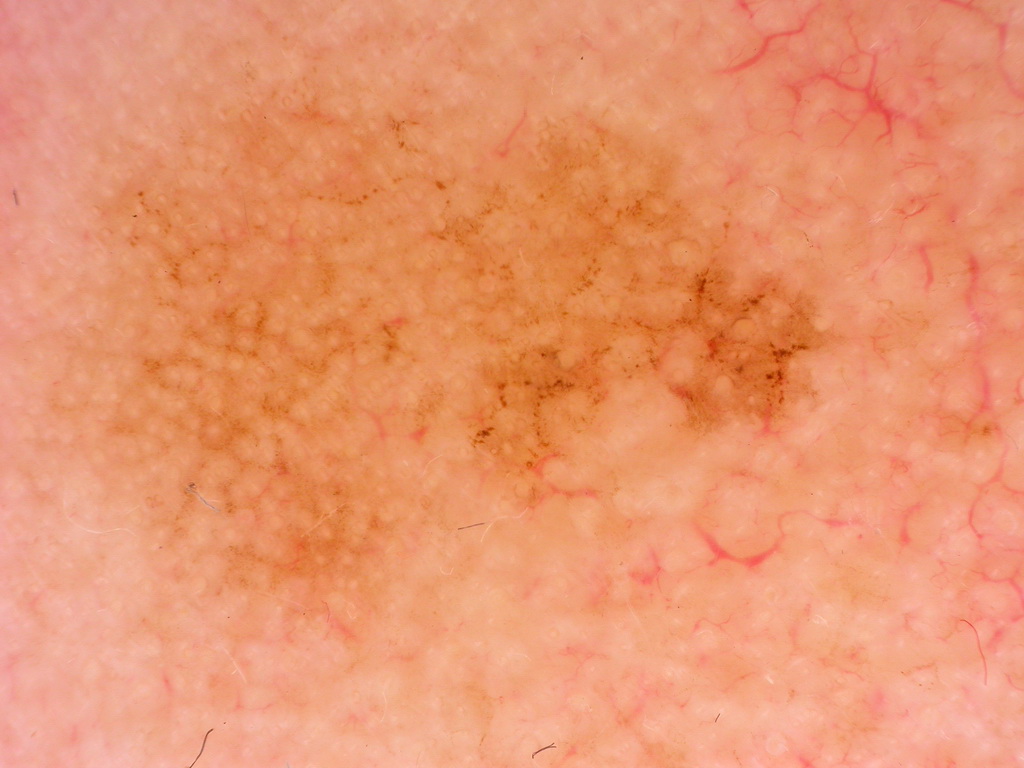Summary:
A dermoscopic image of a skin lesion. Dermoscopic examination shows no globules, streaks, pigment network, negative network, or milia-like cysts. In (x1, y1, x2, y2) order, the lesion is located at 34, 10, 853, 678.
Conclusion:
Histopathological examination showed a melanoma, a malignancy.